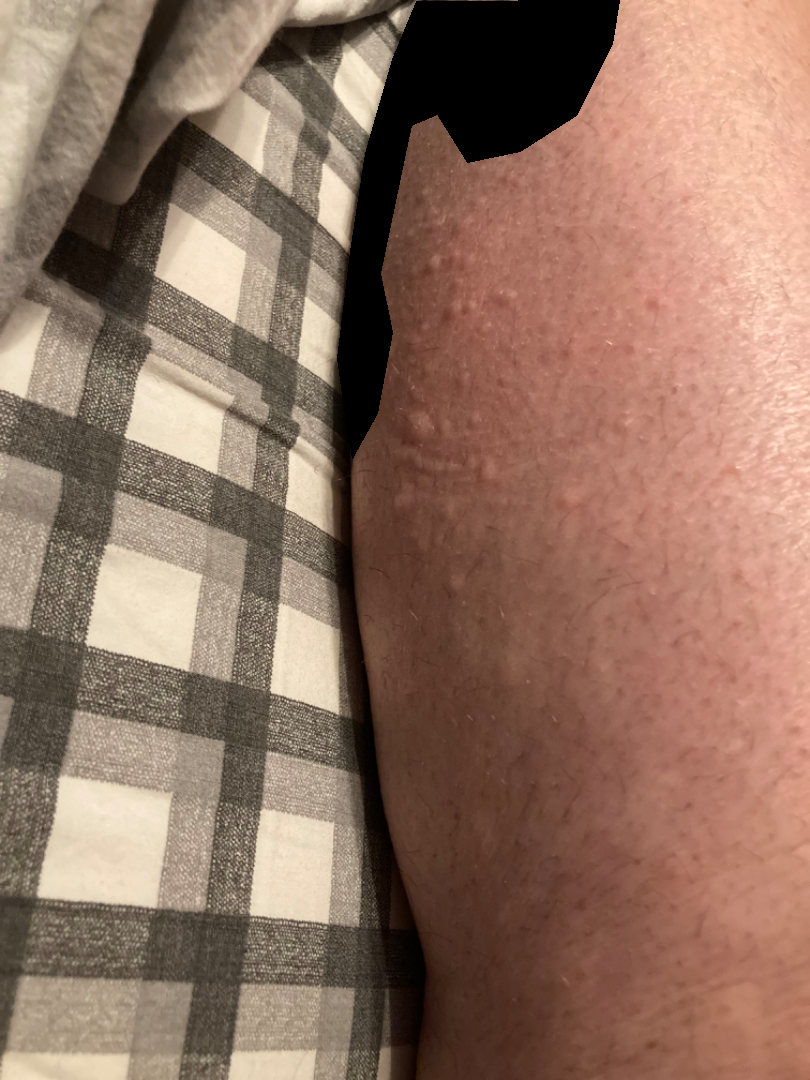contributor: female, age 40–49 | framing: at a distance | anatomic site: arm and leg | differential: the favored diagnosis is Urticaria; with consideration of Eczema; also consider Insect Bite.